The subject is 18–29, female. A close-up photograph. The condition has been present for about one day. Located on the leg. The patient described the issue as a rash. The contributor reports itching. No associated systemic symptoms reported — 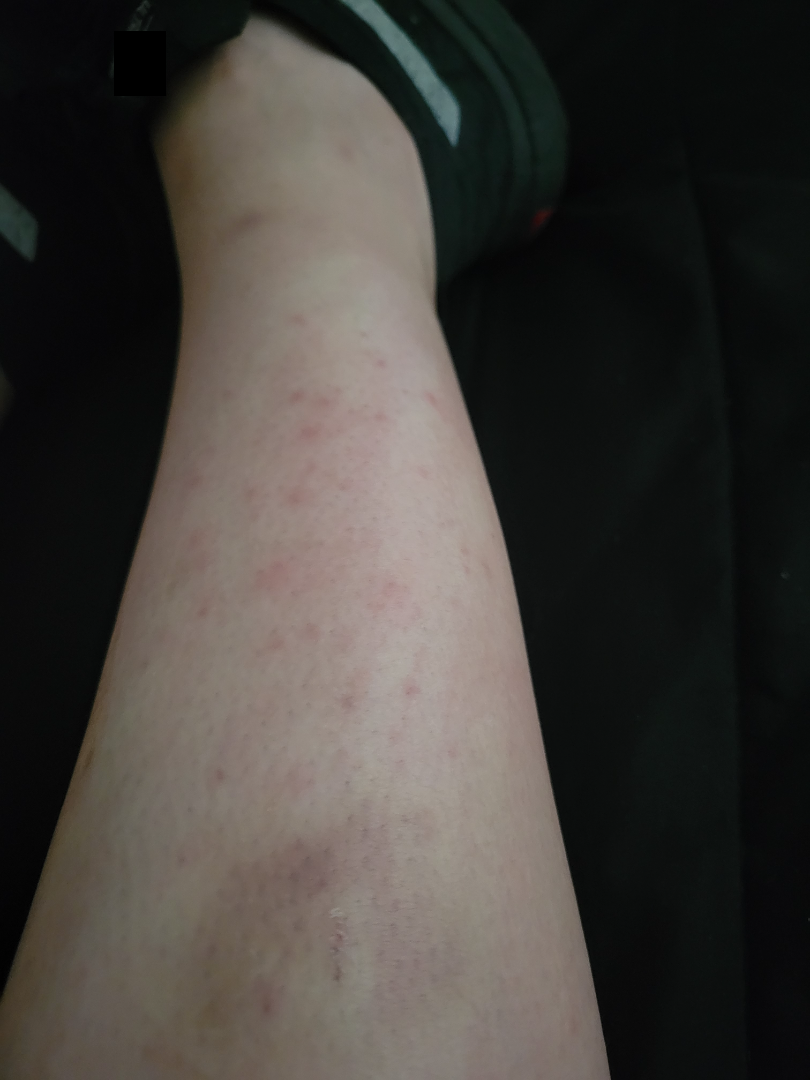| feature | finding |
|---|---|
| assessment | not assessable |